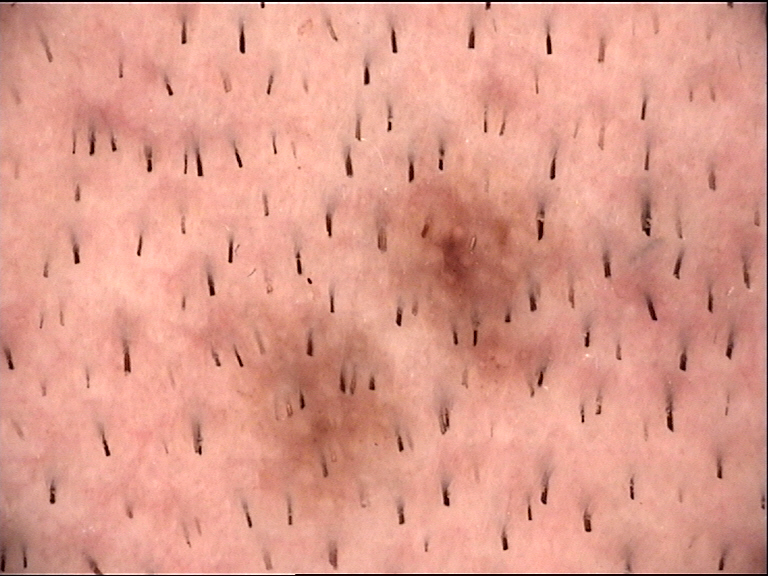diagnostic label=Miescher nevus (expert consensus).